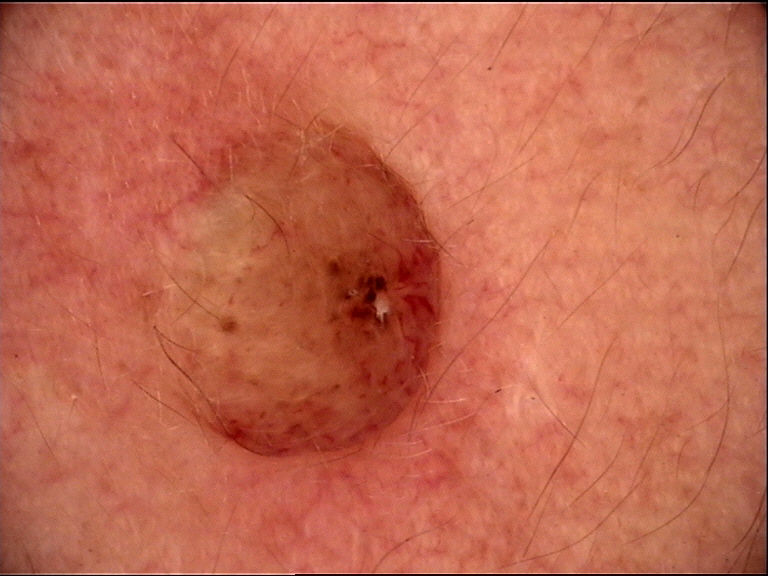<dermoscopy>
  <diagnosis>
    <name>dermal nevus</name>
    <code>db</code>
    <malignancy>benign</malignancy>
    <super_class>melanocytic</super_class>
    <confirmation>expert consensus</confirmation>
  </diagnosis>
</dermoscopy>